A dermoscopy image of a single skin lesion.
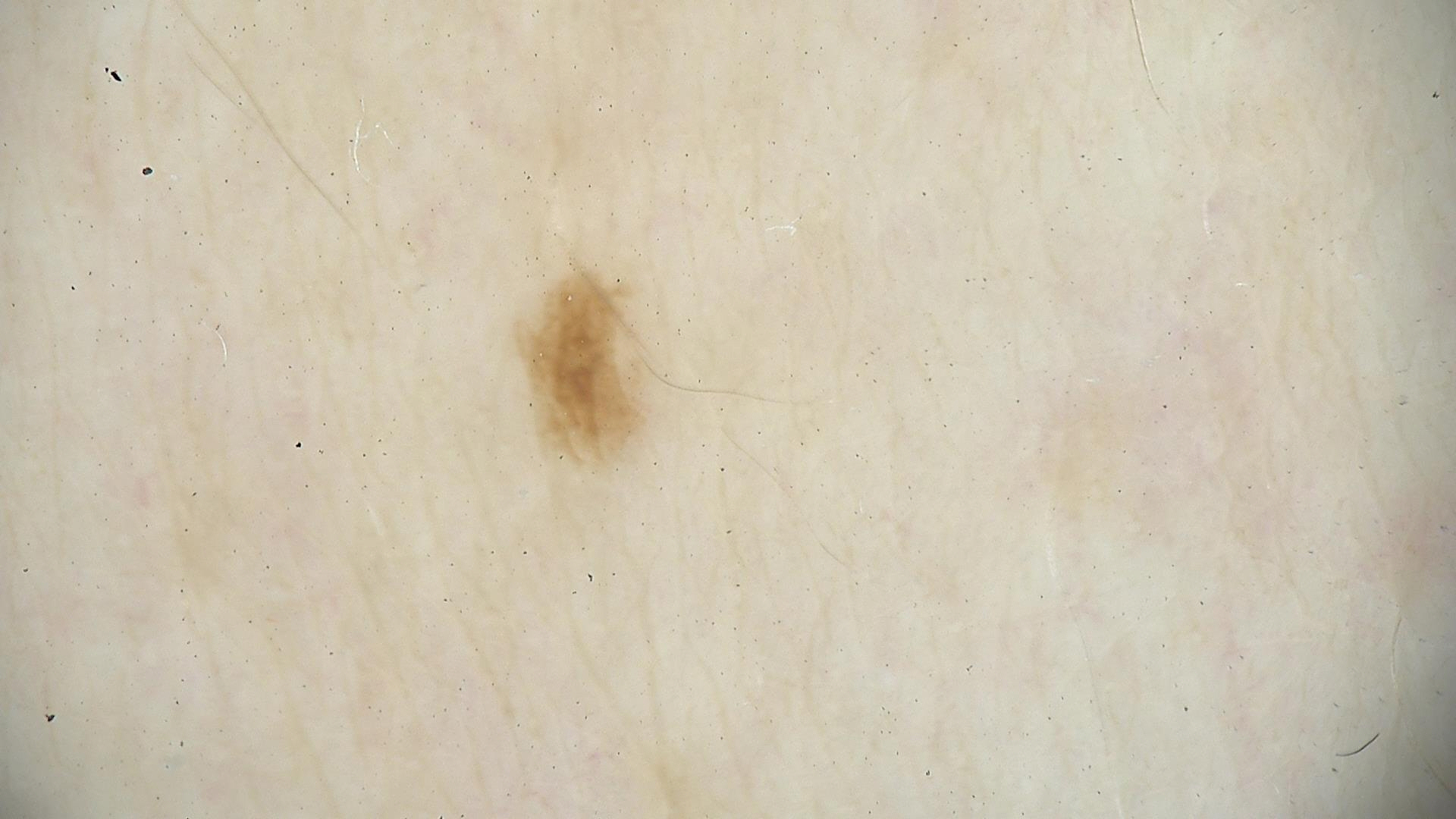Q: What is this lesion?
A: dysplastic junctional nevus (expert consensus)